A dermoscopy image of a single skin lesion: 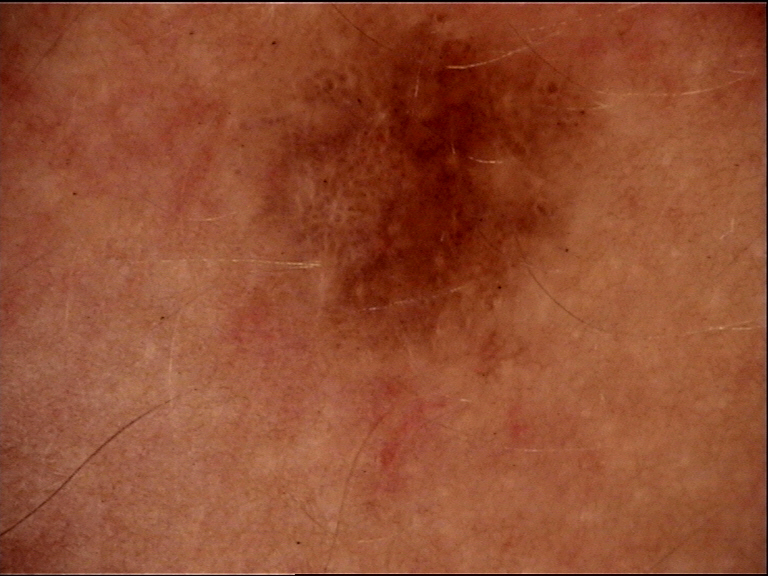The diagnosis was a dysplastic junctional nevus.